A dermoscopic photograph of a skin lesion.
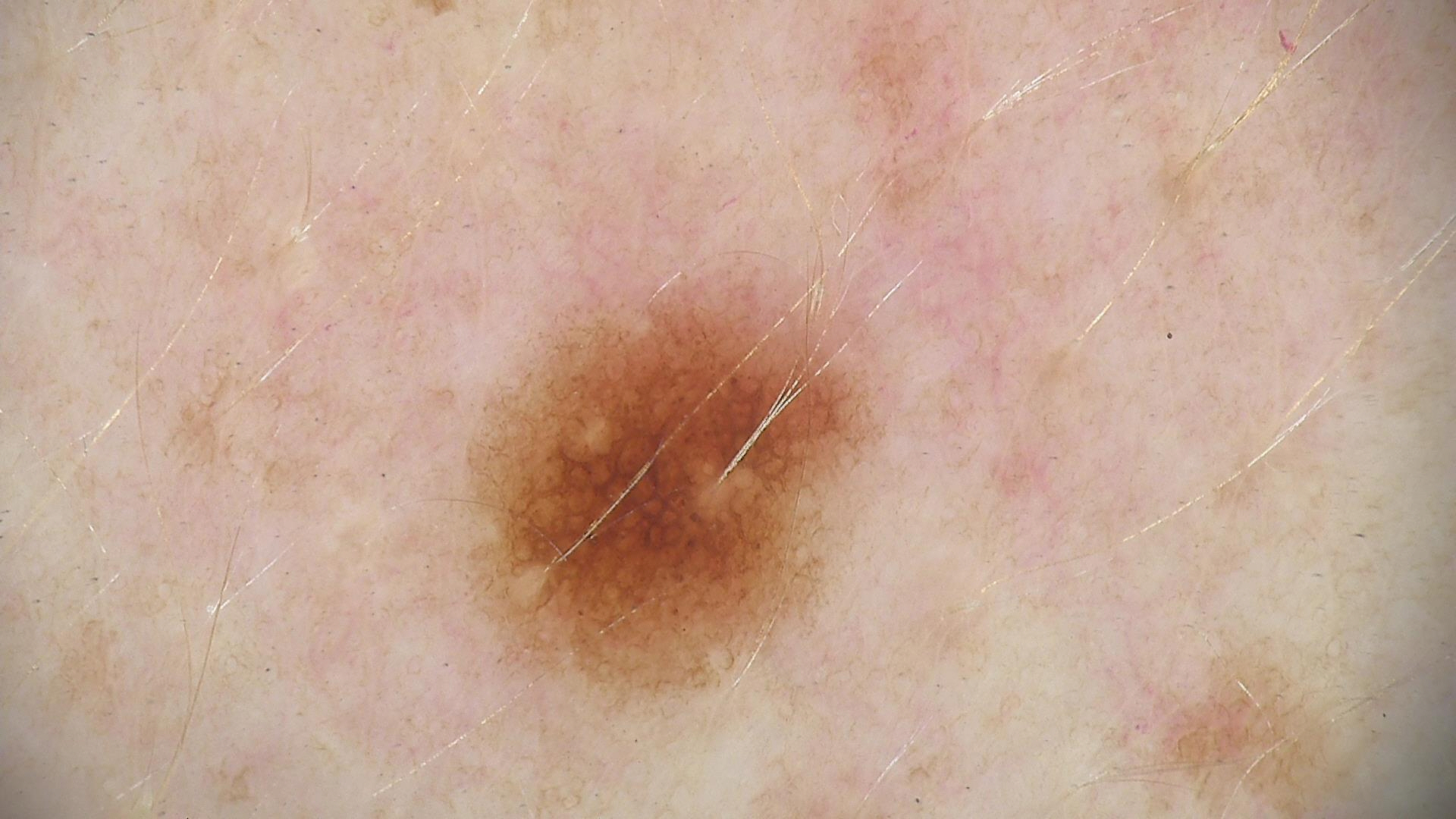Case:
– diagnosis: dysplastic junctional nevus (expert consensus)